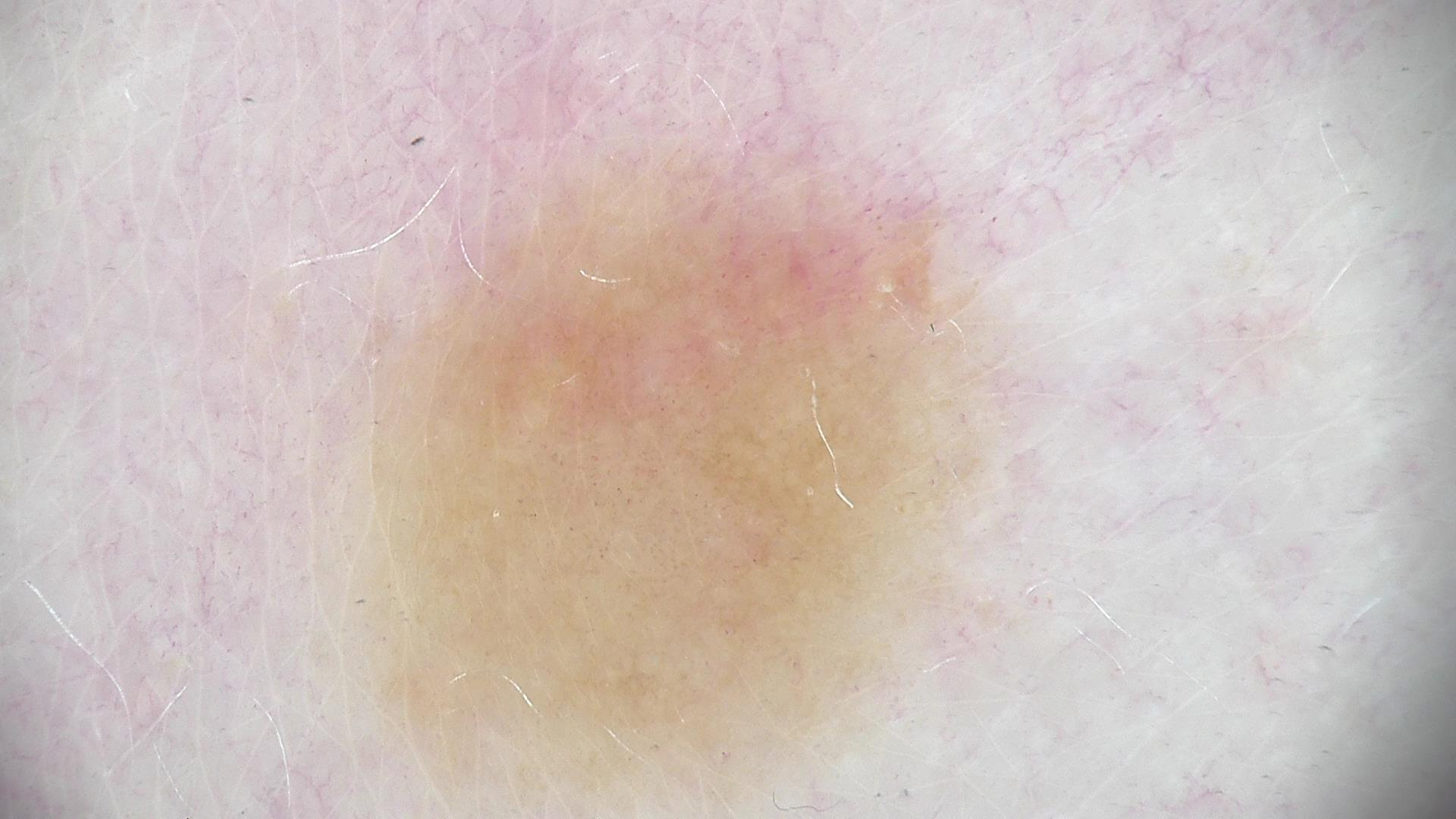assessment = dysplastic junctional nevus (expert consensus).